A wide-field clinical photograph of a skin lesion · a female patient in their 50s: 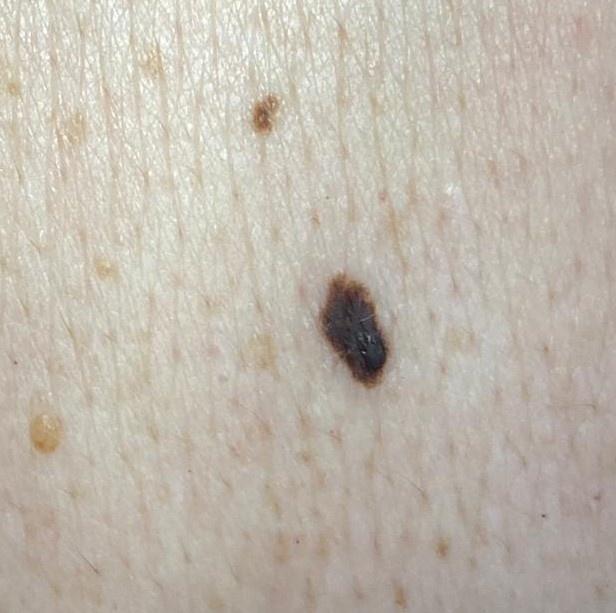Located on the trunk.
On biopsy, the diagnosis was a nevus.